A skin lesion imaged with a dermatoscope.
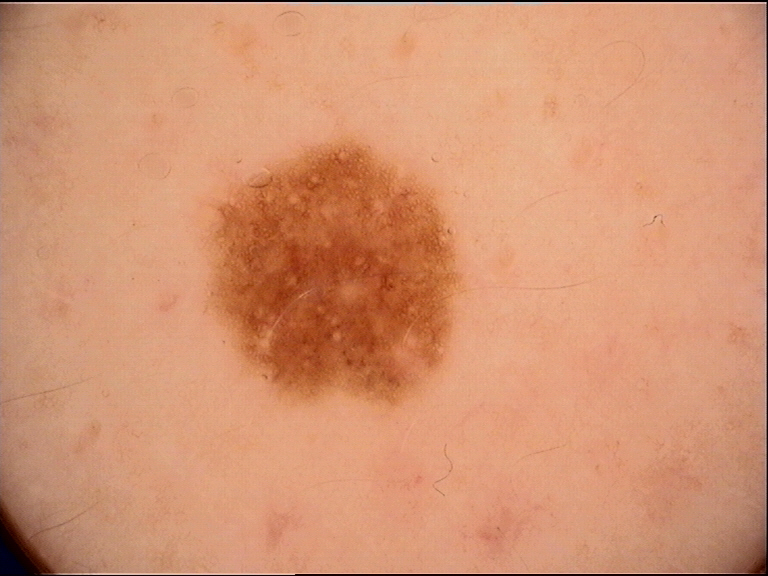| key | value |
|---|---|
| diagnostic label | dysplastic junctional nevus (expert consensus) |